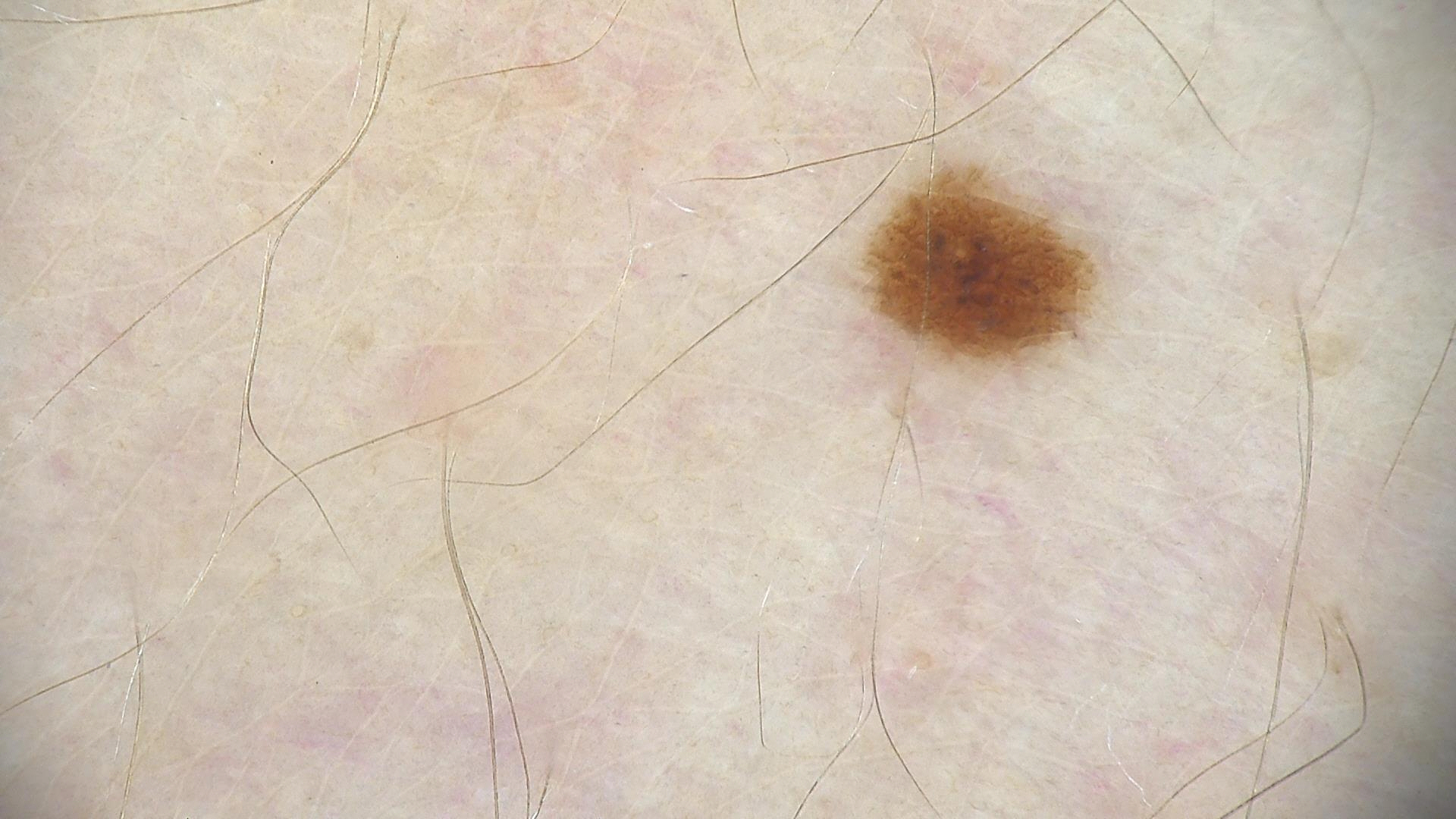Findings:
* label · dysplastic junctional nevus (expert consensus)